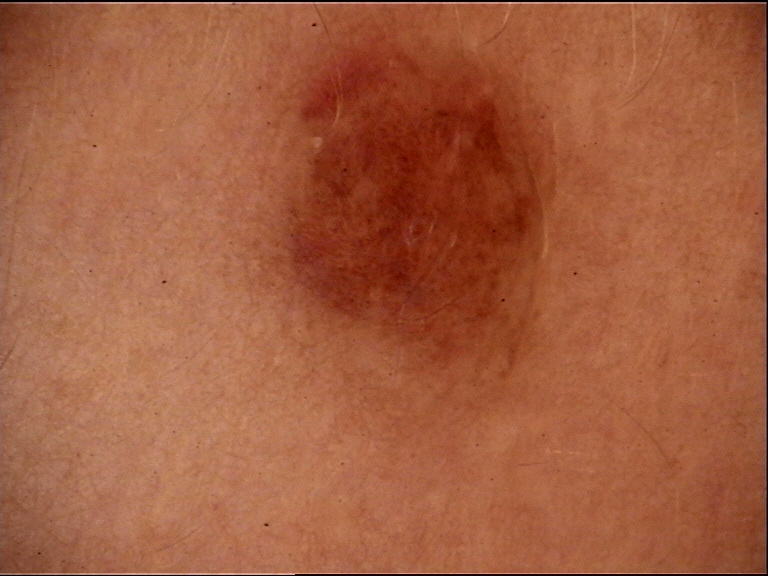Case:
* diagnostic label — dysplastic compound nevus (expert consensus)